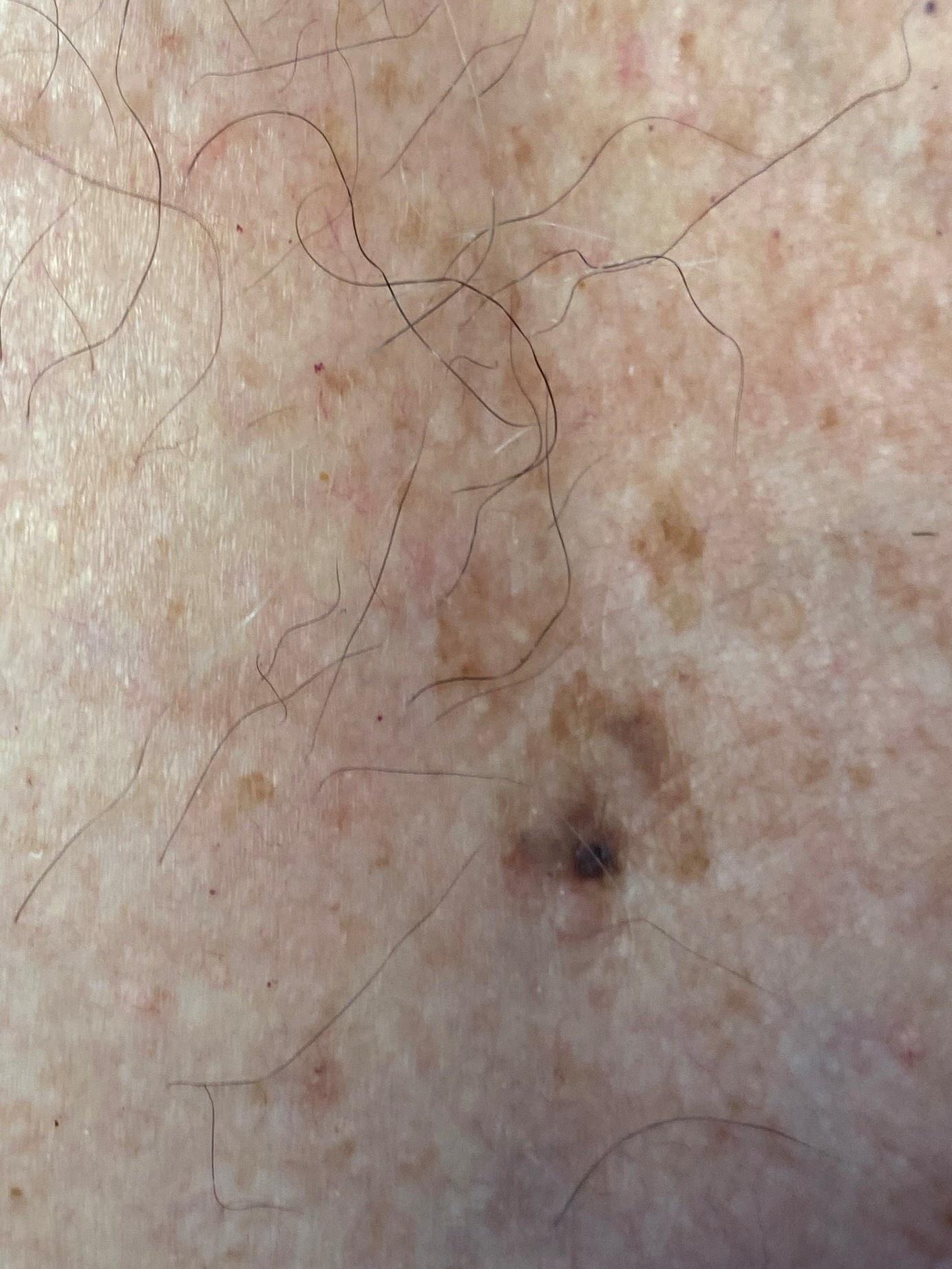Q: What kind of image is this?
A: clinical photo (overview)
Q: What Fitzpatrick skin type was recorded?
A: II
Q: Who is the patient?
A: male, aged 83 or older
Q: What is this lesion?
A: Seborrheic keratosis (biopsy-proven)